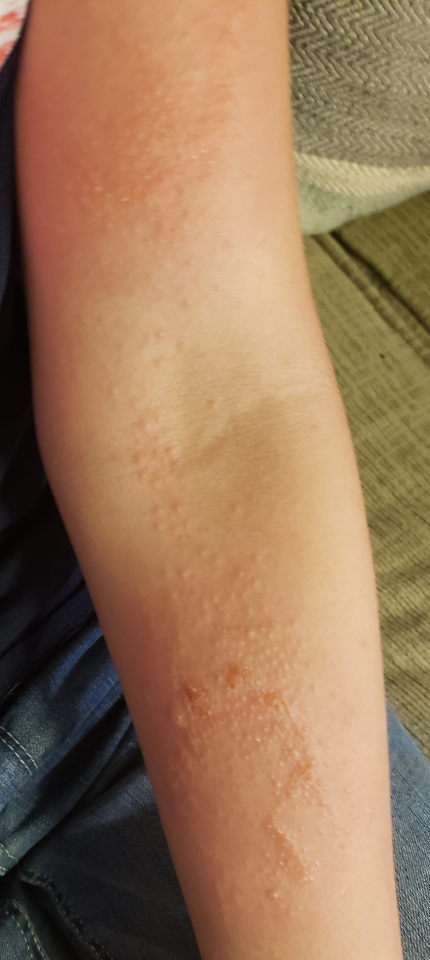{"differential": {"leading": ["Allergic Contact Dermatitis"], "considered": ["Impetigo"]}}